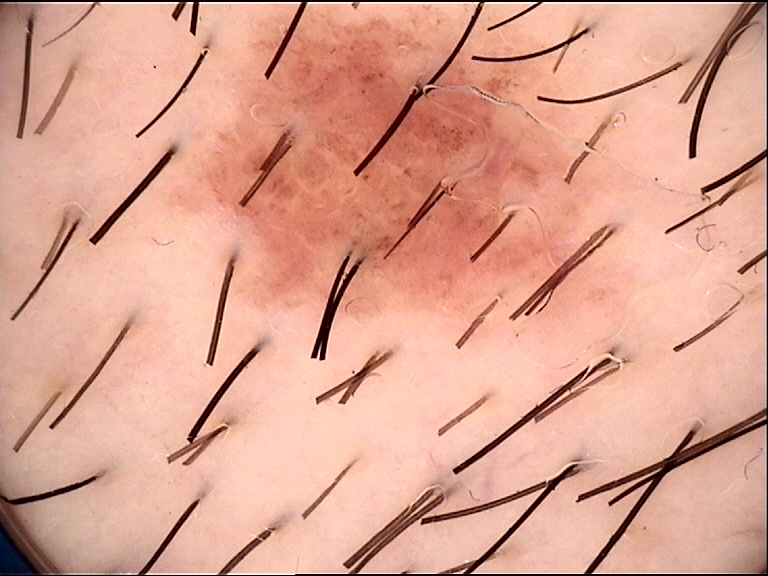Impression: Labeled as a dysplastic compound nevus.